A male subject aged around 70. A dermoscopic close-up of a skin lesion — 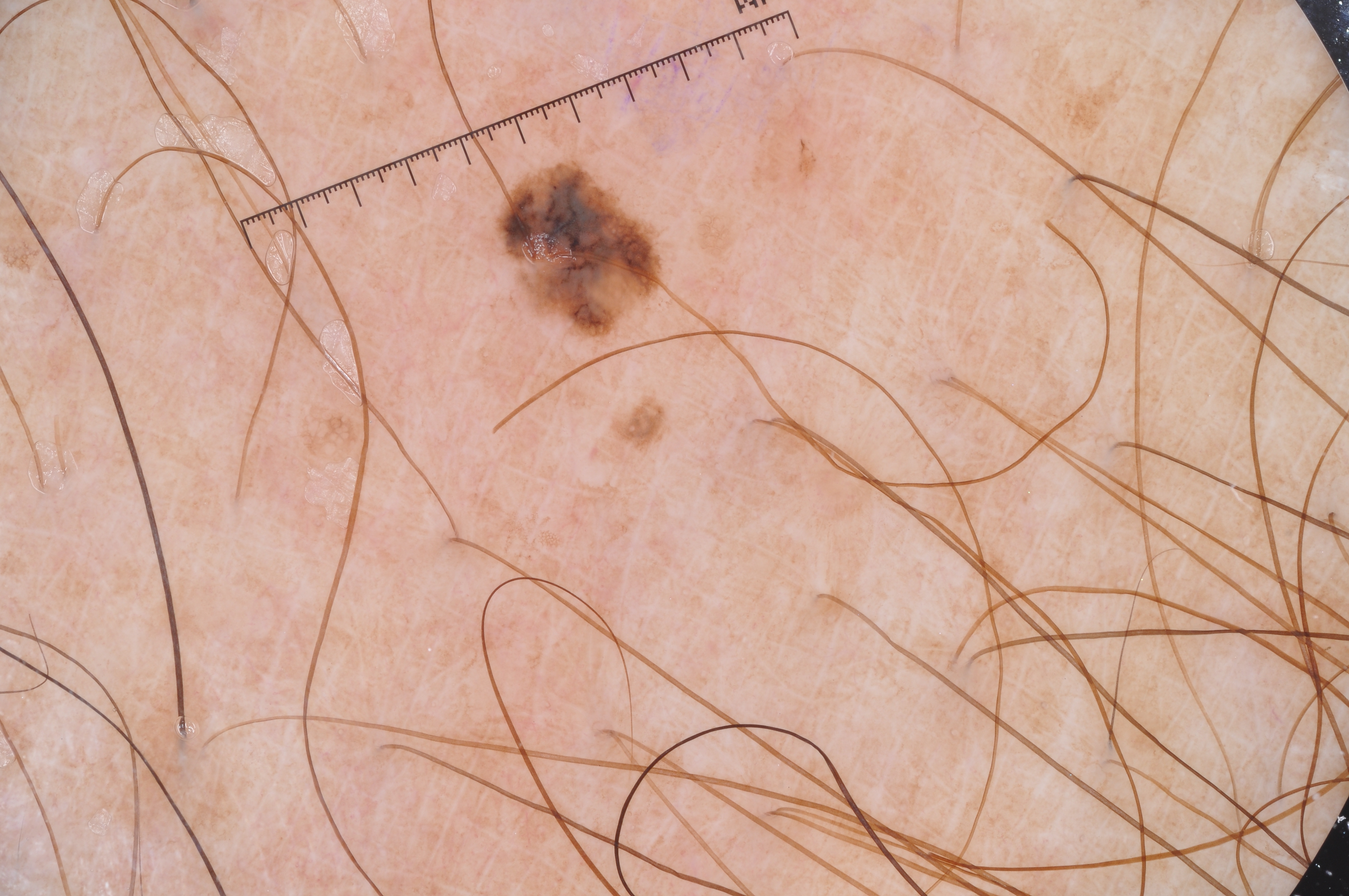{
  "lesion_extent": "small",
  "dermoscopic_features": {
    "present": [
      "pigment network"
    ],
    "absent": [
      "streaks",
      "milia-like cysts",
      "negative network"
    ]
  },
  "lesion_location": {
    "bbox_xyxy": [
      495,
      155,
      668,
      345
    ]
  },
  "diagnosis": {
    "name": "melanoma",
    "malignancy": "malignant",
    "lineage": "melanocytic",
    "provenance": "histopathology"
  }
}